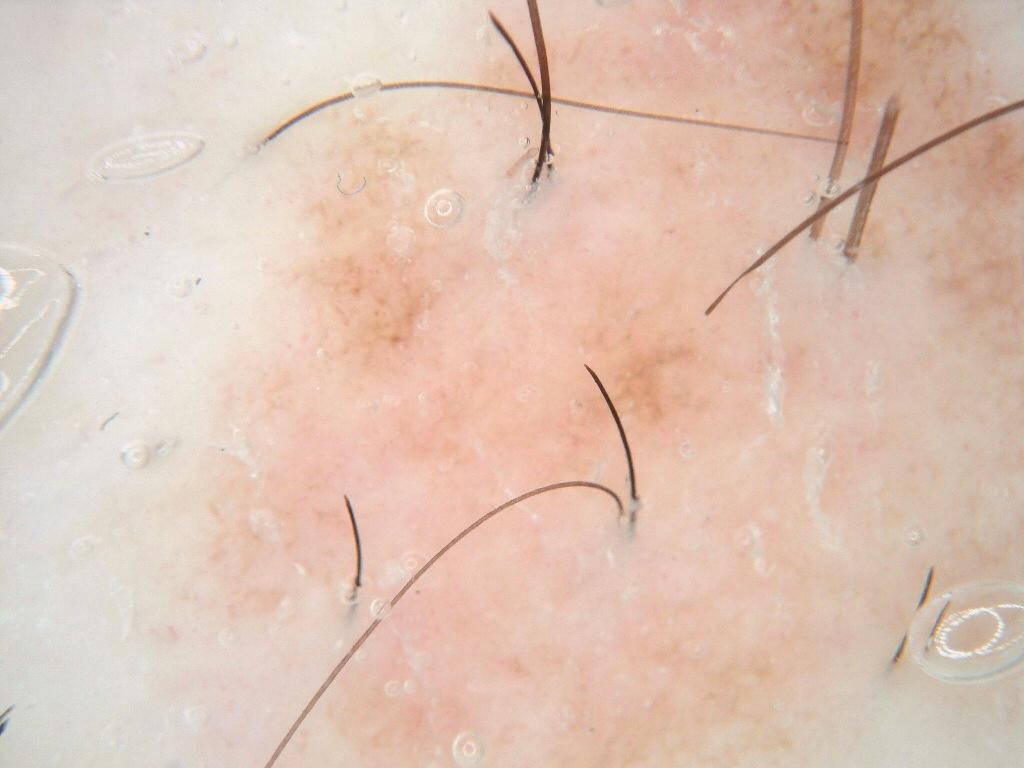| feature | finding |
|---|---|
| imaging | dermoscopic image |
| lesion size | ~77% of the field |
| lesion margin | reaches the image border |
| lesion bbox | 153 0 1017 764 |
| diagnosis | a benign lesion |